The lesion involves the arm and back of the hand. This image was taken at an angle — 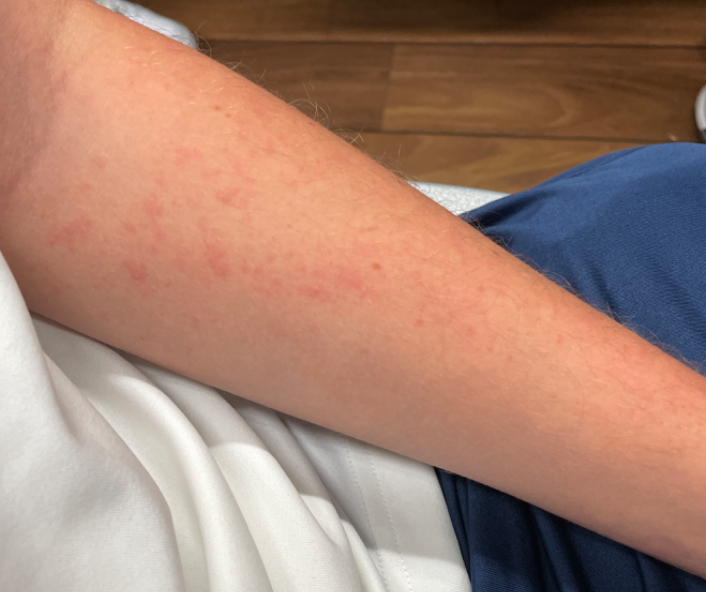• lesion texture — raised or bumpy
• present for — less than one week
• impression — one reviewing dermatologist: the differential is split between Eczema, Allergic Contact Dermatitis and Irritant Contact Dermatitis